A male subject roughly 40 years of age. The patient is skin type III. A dermoscopic photograph of a skin lesion — 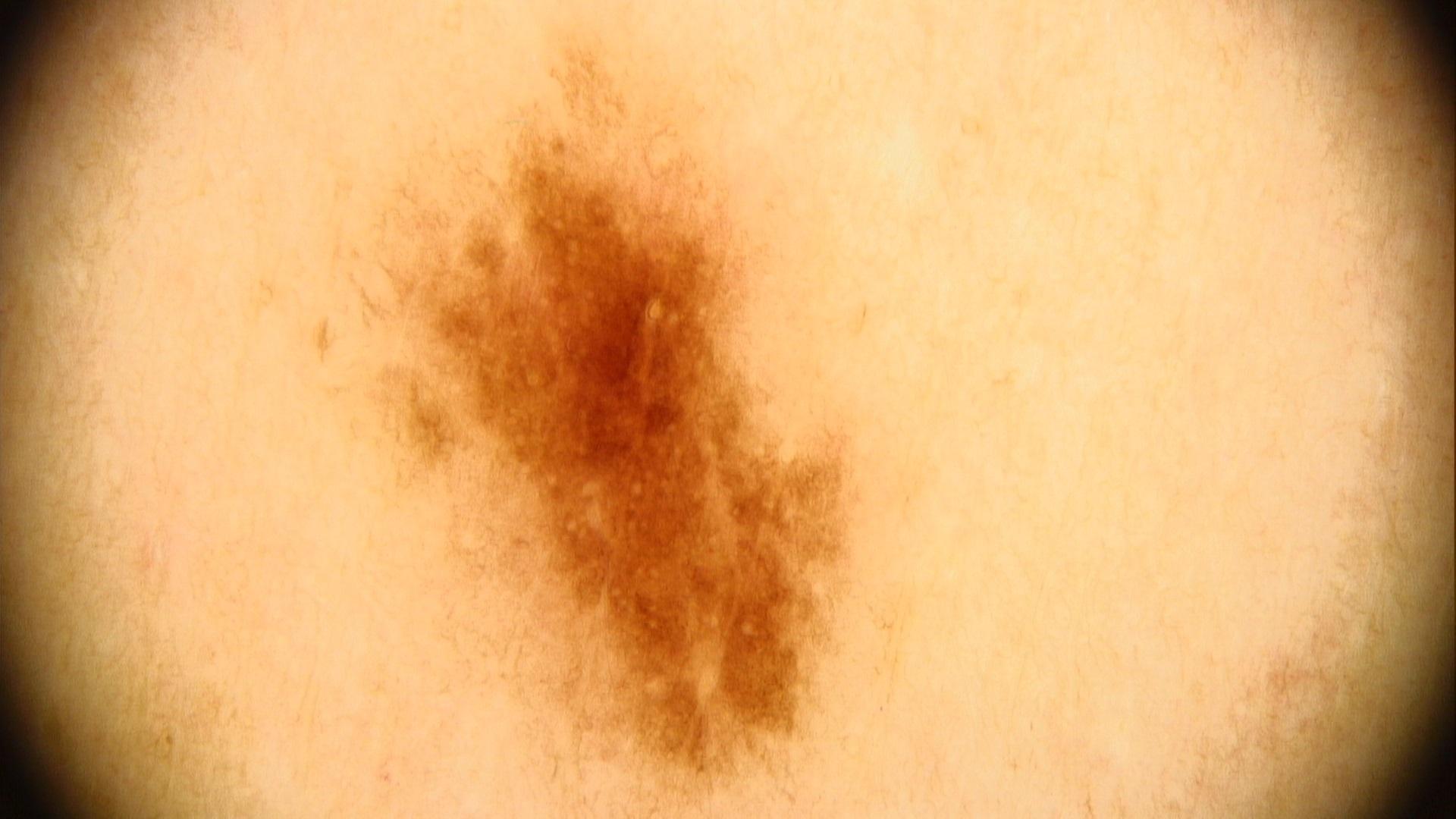The lesion was found on the trunk, specifically the posterior trunk.
The diagnostic impression was a melanocytic lesion — a nevus.